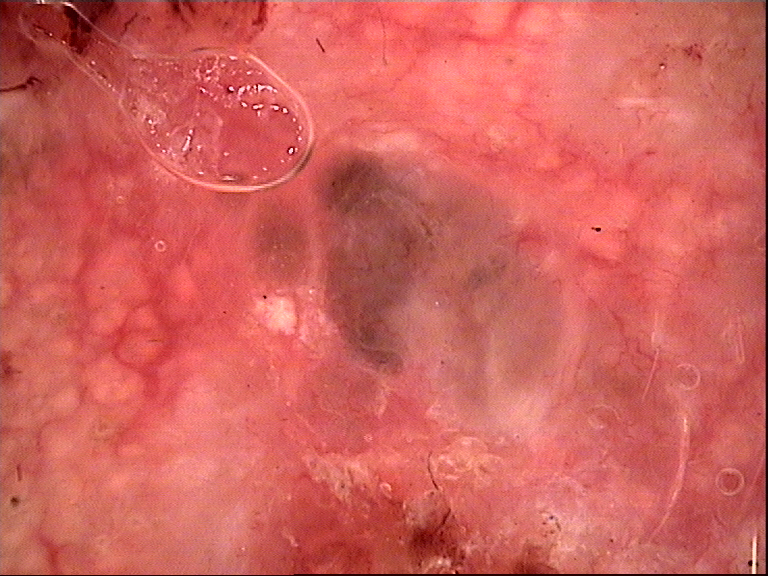image: dermoscopy; classification: keratinocytic; class: basal cell carcinoma (biopsy-proven).